Dermoscopy of a skin lesion: 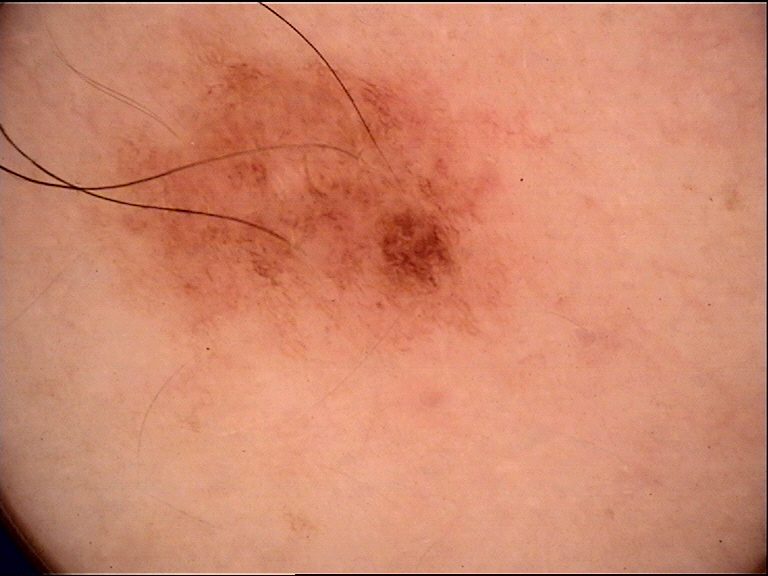Consistent with a dysplastic junctional nevus.